Dermoscopy of a skin lesion: 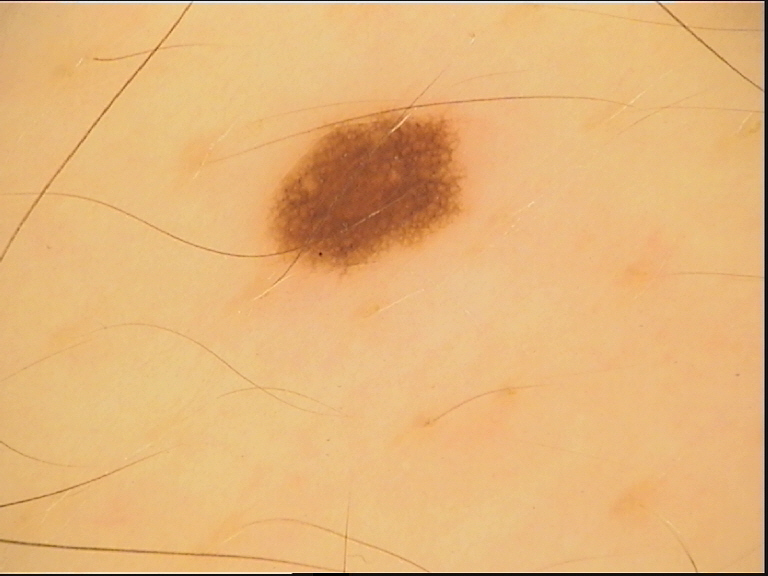  diagnosis:
    name: dysplastic junctional nevus
    code: jd
    malignancy: benign
    super_class: melanocytic
    confirmation: expert consensus